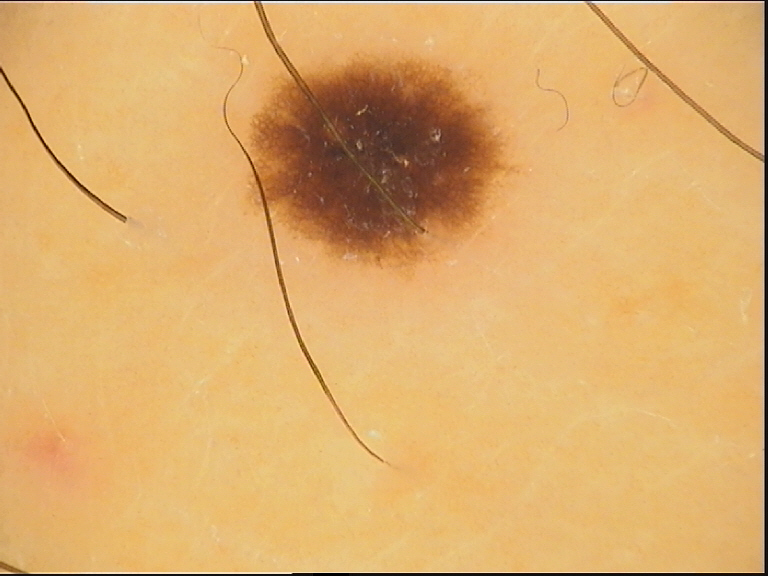imaging = dermatoscopy, subtype = banal, label = junctional nevus (expert consensus).